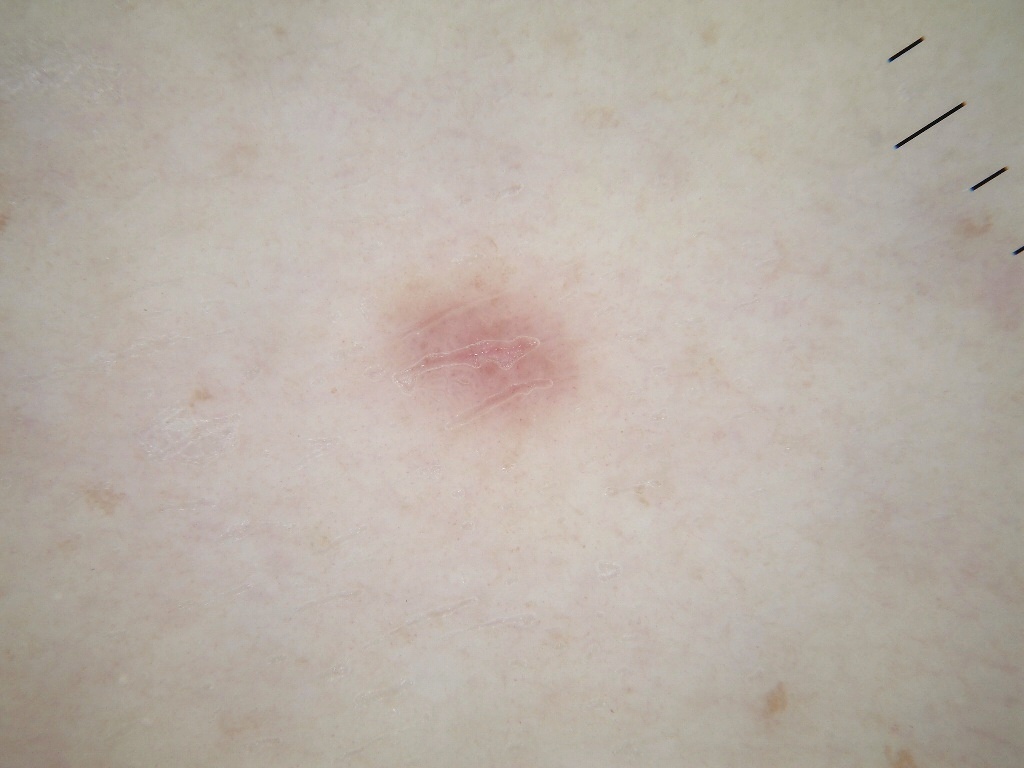Case summary:
- subject — female, aged approximately 30
- imaging — dermoscopy of a skin lesion
- size — small
- absent dermoscopic findings — milia-like cysts, pigment network, negative network, streaks, and globules
- location — bbox=[371, 255, 594, 447]
- impression — a melanocytic nevus, a benign skin lesion